A skin lesion imaged with a dermatoscope:
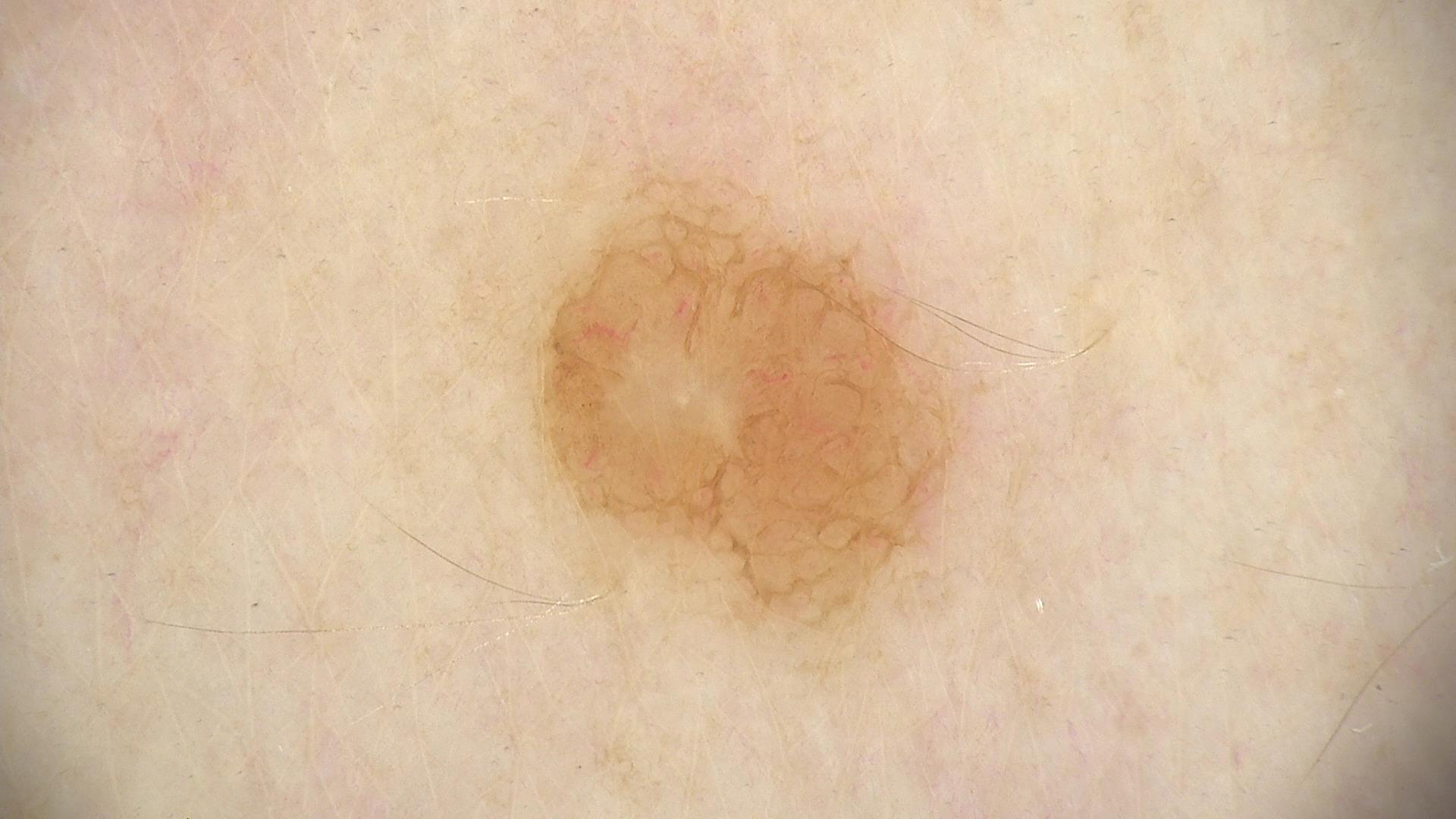Diagnosed as a banal lesion — a compound nevus.